The photograph is a close-up of the affected area: 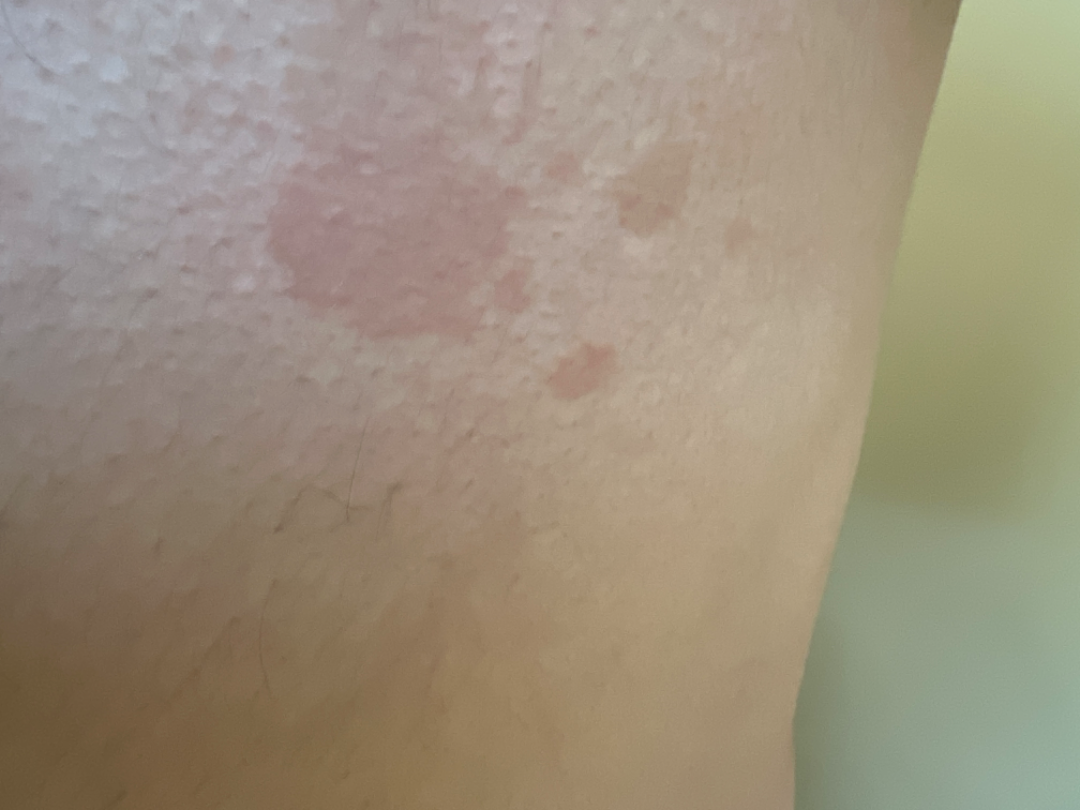Findings:
Diagnostic features were not clearly distinguishable in this photograph.